A female patient 58 years of age · the patient was assessed as FST I:
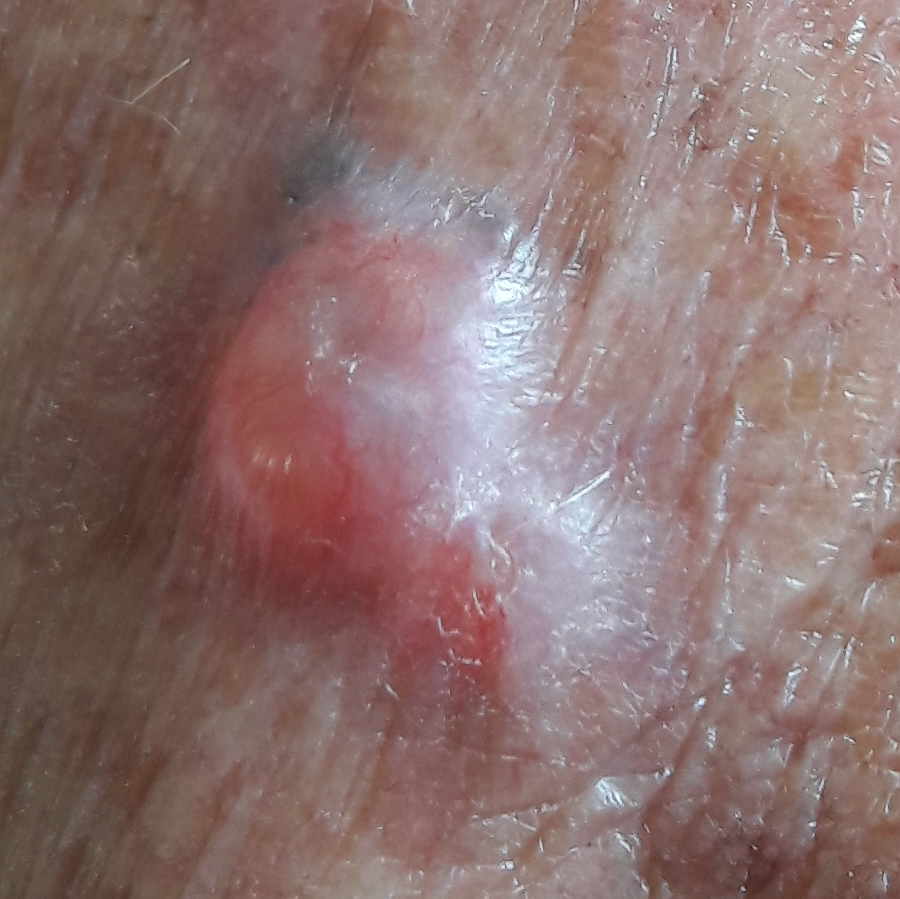| feature | finding |
|---|---|
| location | a hand |
| diameter | 11 × 8 mm |
| pathology | basal cell carcinoma (biopsy-proven) |